The patient indicates the lesion is raised or bumpy. The lesion involves the back of the torso, head or neck and front of the torso. Self-categorized by the patient as a rash. This image was taken at a distance. The condition has been present for less than one week. Symptoms reported: itching: 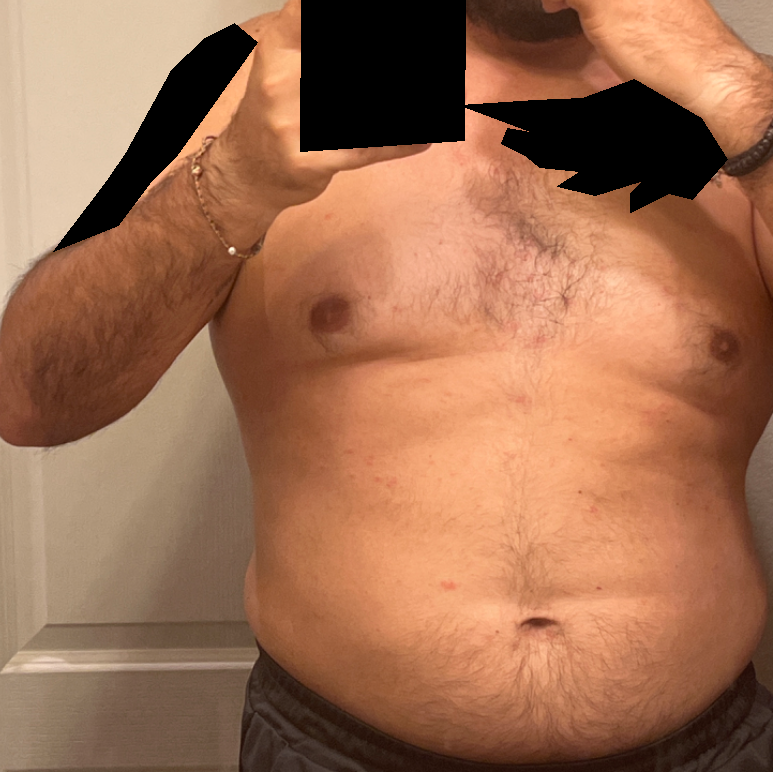Q: What conditions are considered?
A: a single dermatologist reviewed the case: Acute dermatitis and Itchy skin eruption were considered with similar weight; lower on the differential is Viral Exanthem